A clinical photograph showing a skin lesion. A male subject 78 years of age: 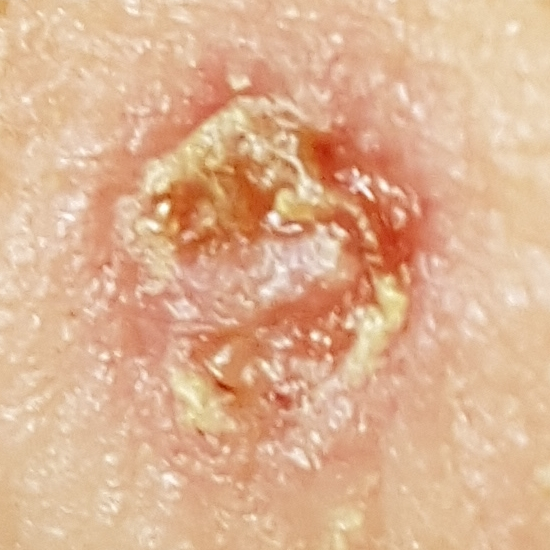Summary:
Located on the face. The patient describes that the lesion has grown, itches, hurts, and has bled, but has not changed and is not elevated.
Diagnosis:
Histopathology confirmed a basal cell carcinoma.